The patient is a male aged 73-77 · a dermoscopy image of a single skin lesion.
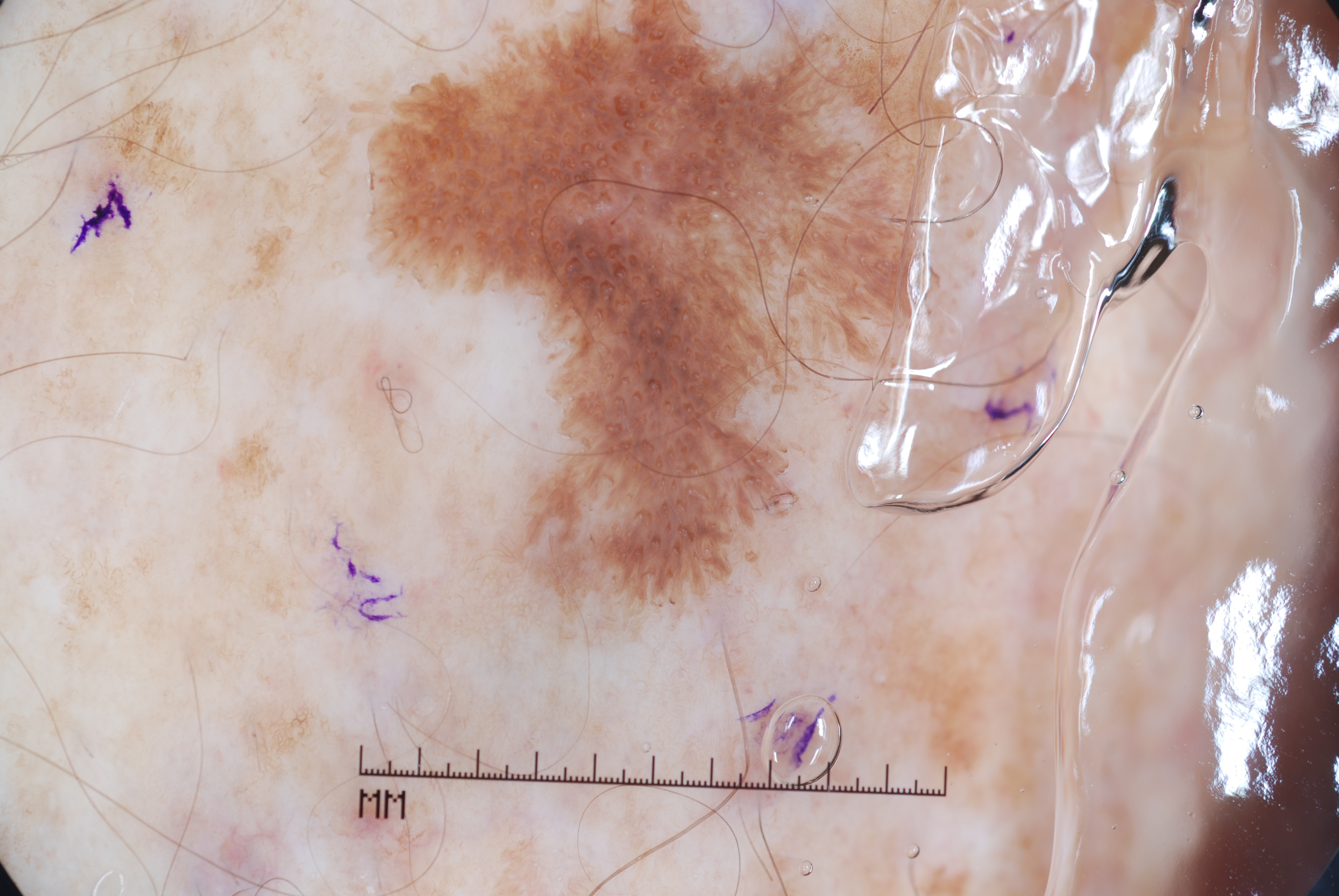<lesion>
  <lesion_extent>large</lesion_extent>
  <lesion_location>
    <bbox_xyxy>303, 6, 1018, 662</bbox_xyxy>
  </lesion_location>
  <dermoscopic_features>
    <present>milia-like cysts</present>
    <absent>negative network, streaks, pigment network</absent>
  </dermoscopic_features>
  <diagnosis>
    <name>seborrheic keratosis</name>
    <malignancy>benign</malignancy>
    <lineage>keratinocytic</lineage>
    <provenance>clinical</provenance>
  </diagnosis>
</lesion>